A dermoscopic image of a skin lesion.
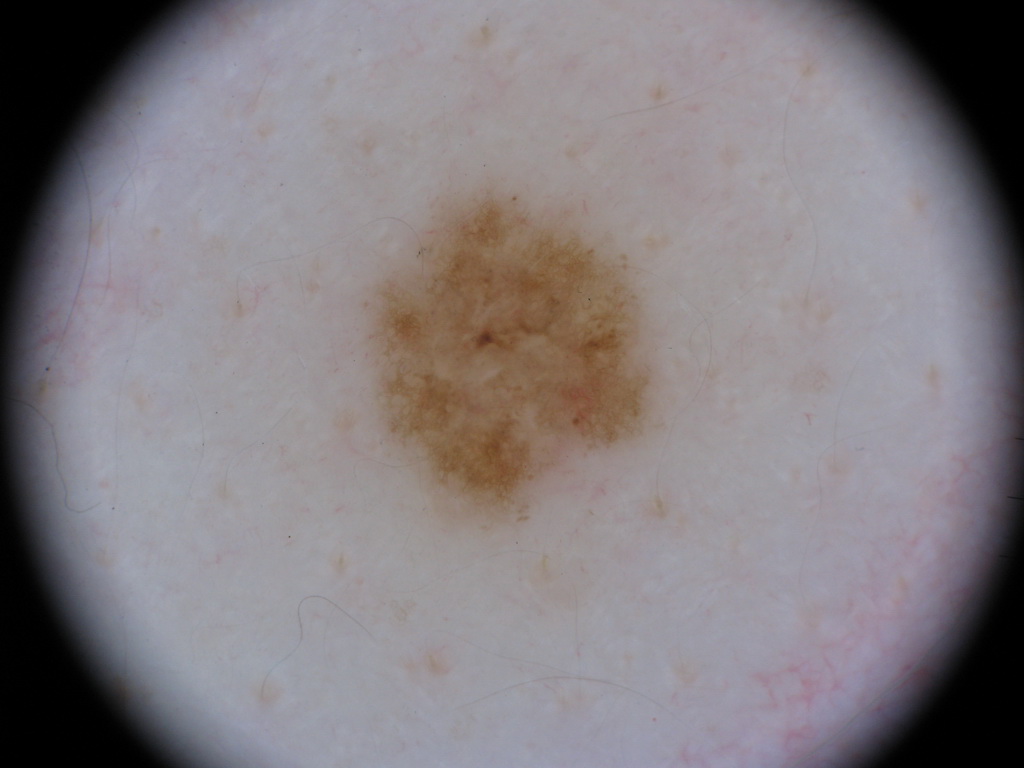lesion bbox: left=353, top=169, right=678, bottom=538
impression: a melanocytic nevus, a benign skin lesion